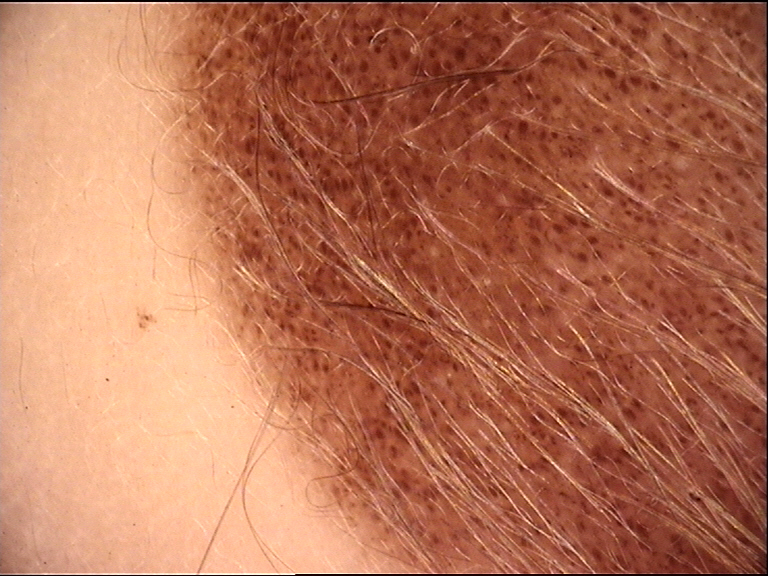label — congenital junctional nevus (expert consensus).